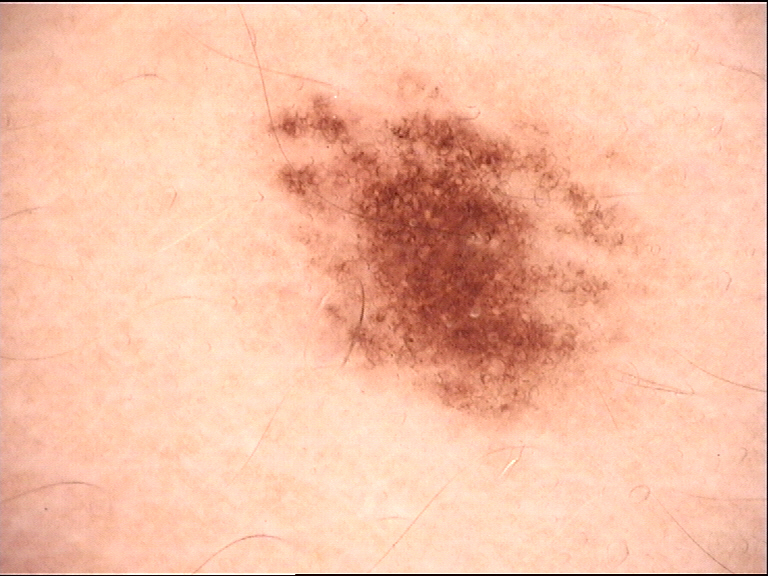Case:
– diagnosis · junctional nevus (expert consensus)